Located on the back of the torso. A close-up photograph. The subject is a male aged 18–29 — 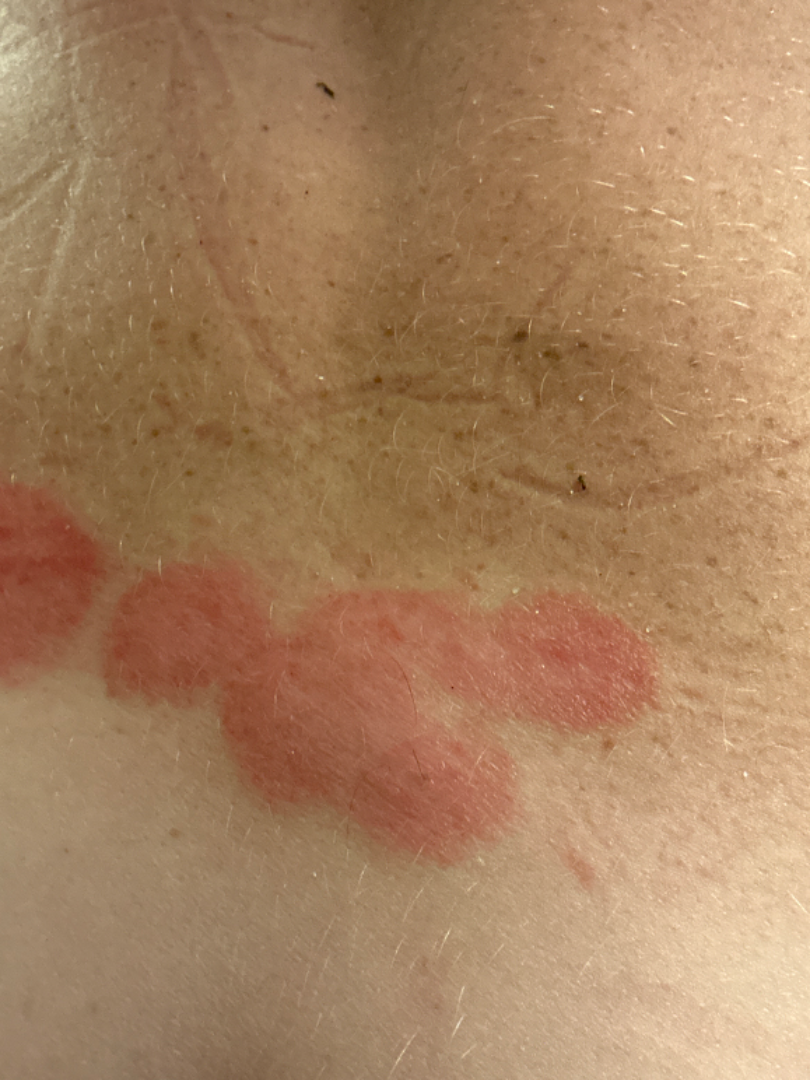Q: Could the case be diagnosed?
A: not assessable